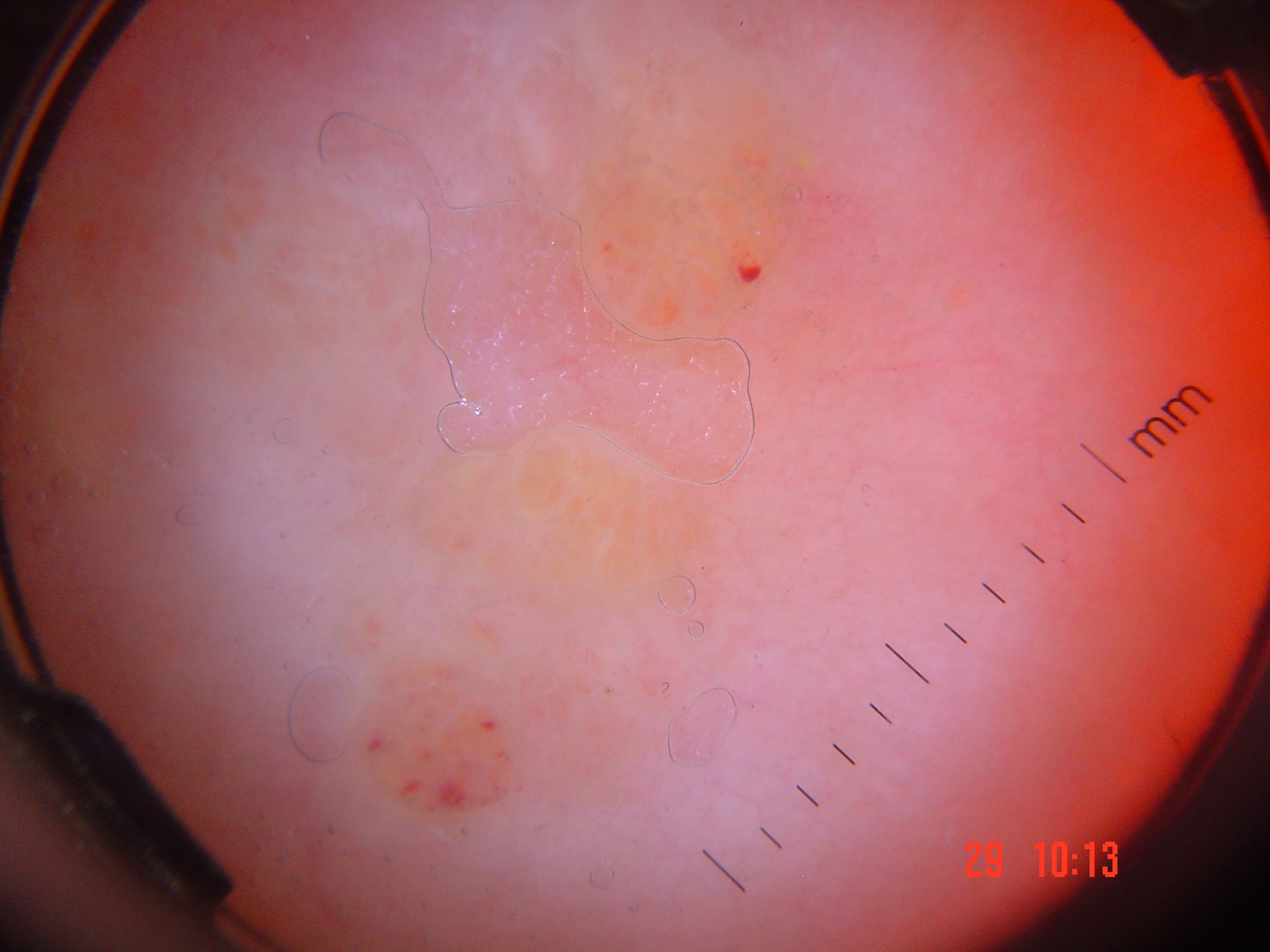Q: What is the imaging modality?
A: dermatoscopy
Q: How is the lesion classified?
A: vascular
Q: What was the diagnostic impression?
A: lymphangioma (expert consensus)